The patient was assessed as Fitzpatrick phototype II; a female patient 63 years of age; a clinical photo of a skin lesion taken with a smartphone:
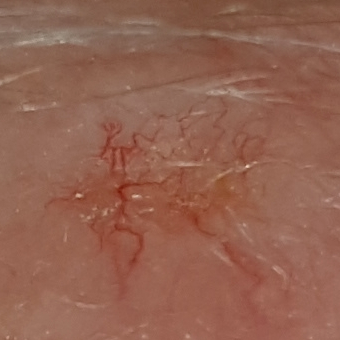The lesion is located on the face.
The lesion measures approximately 7 × 5 mm.
The patient reports no symptoms.
Histopathology confirmed a malignant skin lesion — a basal cell carcinoma.